Dermoscopy of a skin lesion. Recorded as Fitzpatrick skin type II. A female subject approximately 85 years of age or older — 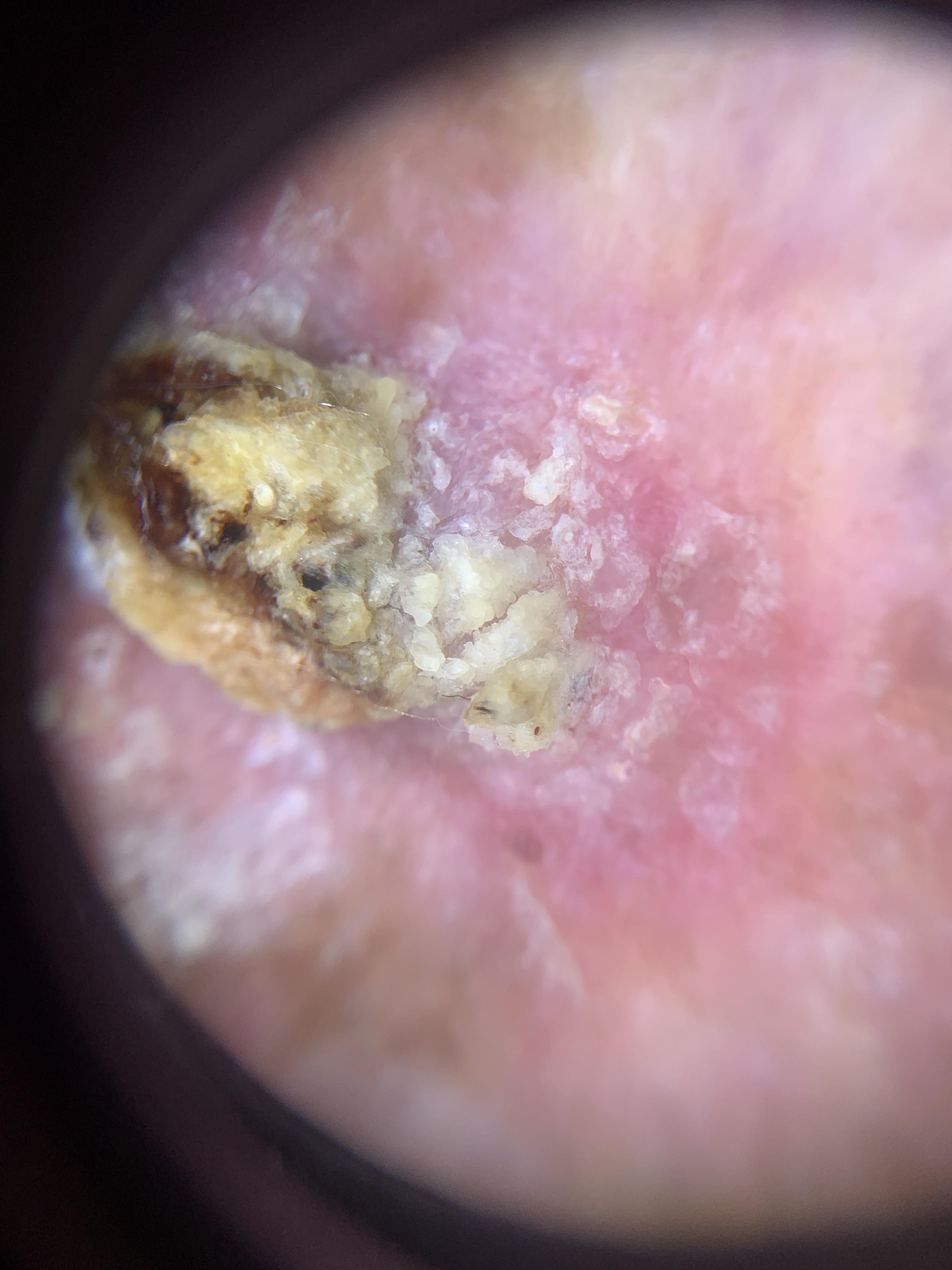<skin_lesion>
  <diagnosis>
    <name>Squamous cell carcinoma</name>
    <malignancy>malignant</malignancy>
    <confirmation>histopathology</confirmation>
    <lineage>epidermal</lineage>
  </diagnosis>
</skin_lesion>